Located on the arm · female subject, age 40–49 · the photo was captured at an angle:
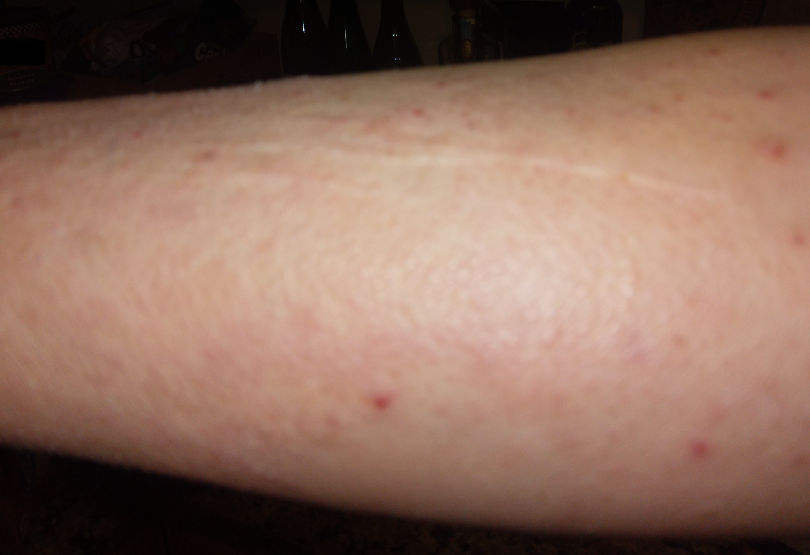Q: What is the dermatologist's impression?
A: reviewed remotely by three dermatologists: the leading consideration is Lichen Simplex Chronicus; also on the differential is Folliculitis; an alternative is Tinea; less probable is Eczema